A dermoscopic image of a skin lesion: 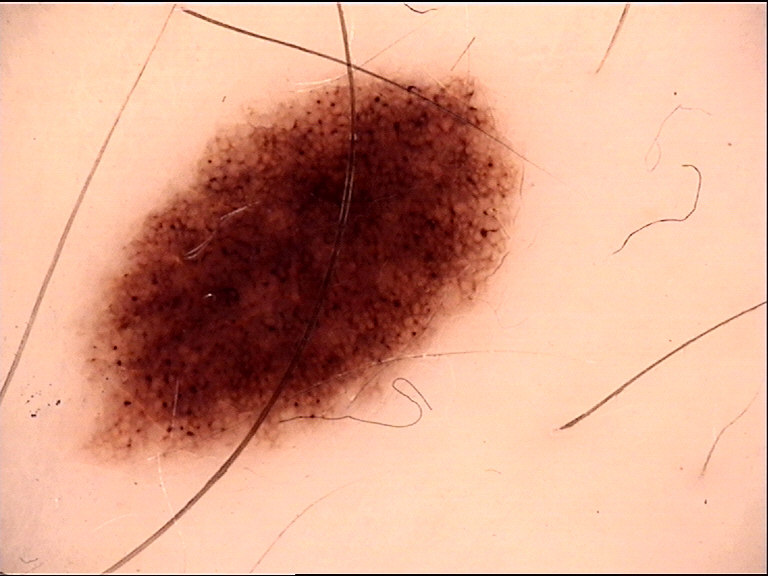Labeled as a dysplastic junctional nevus.